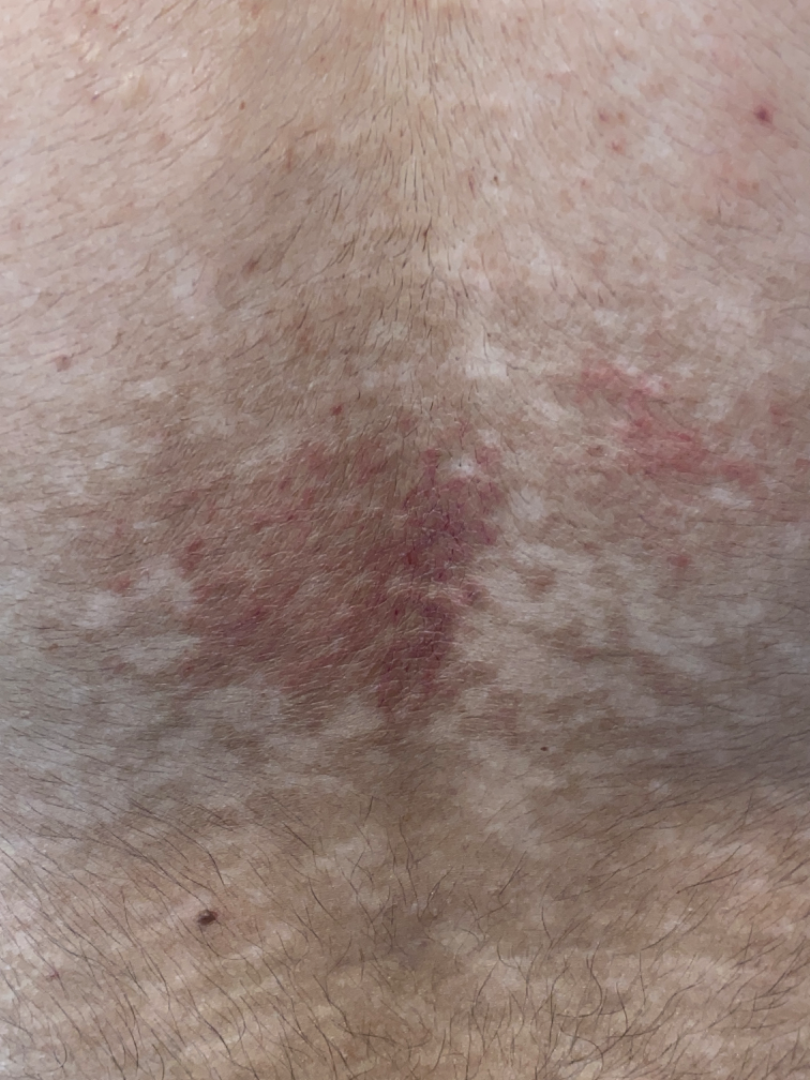On remote review of the image: the leading impression is Erythema ab igne; an alternative is Livedo reticularis.